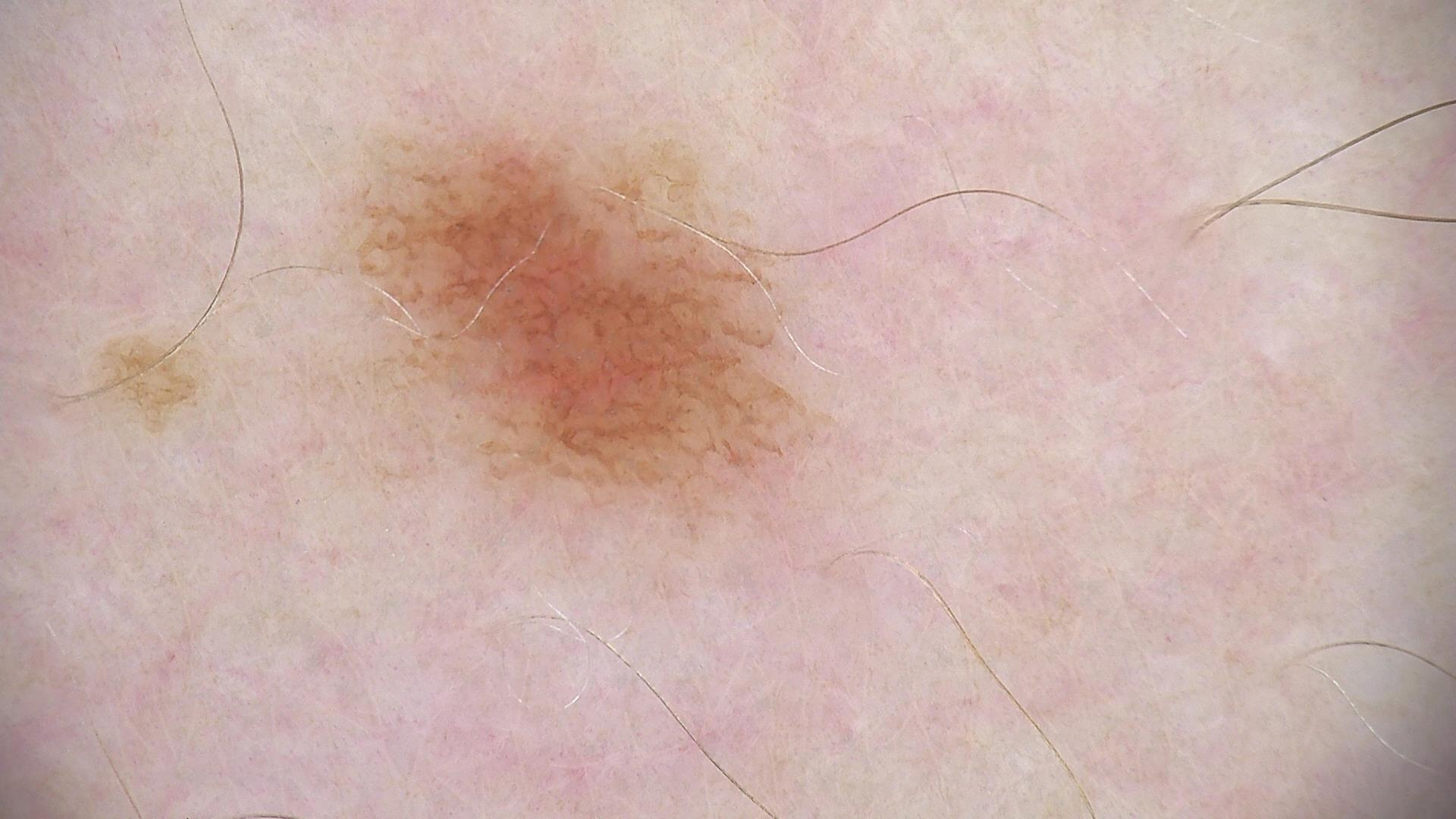Q: What is the diagnosis?
A: dysplastic junctional nevus (expert consensus)